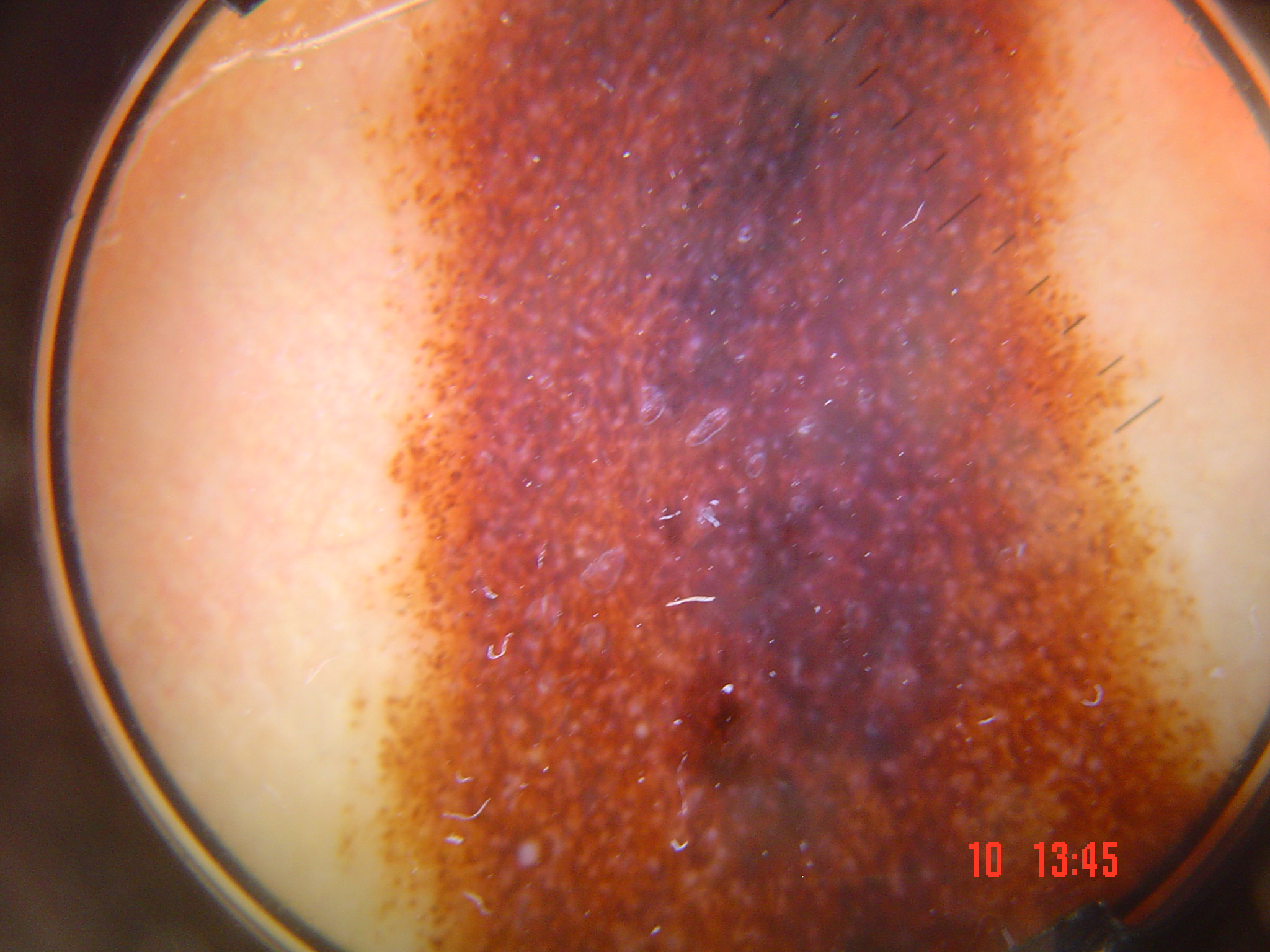Consistent with a banal lesion — a congenital compound nevus.